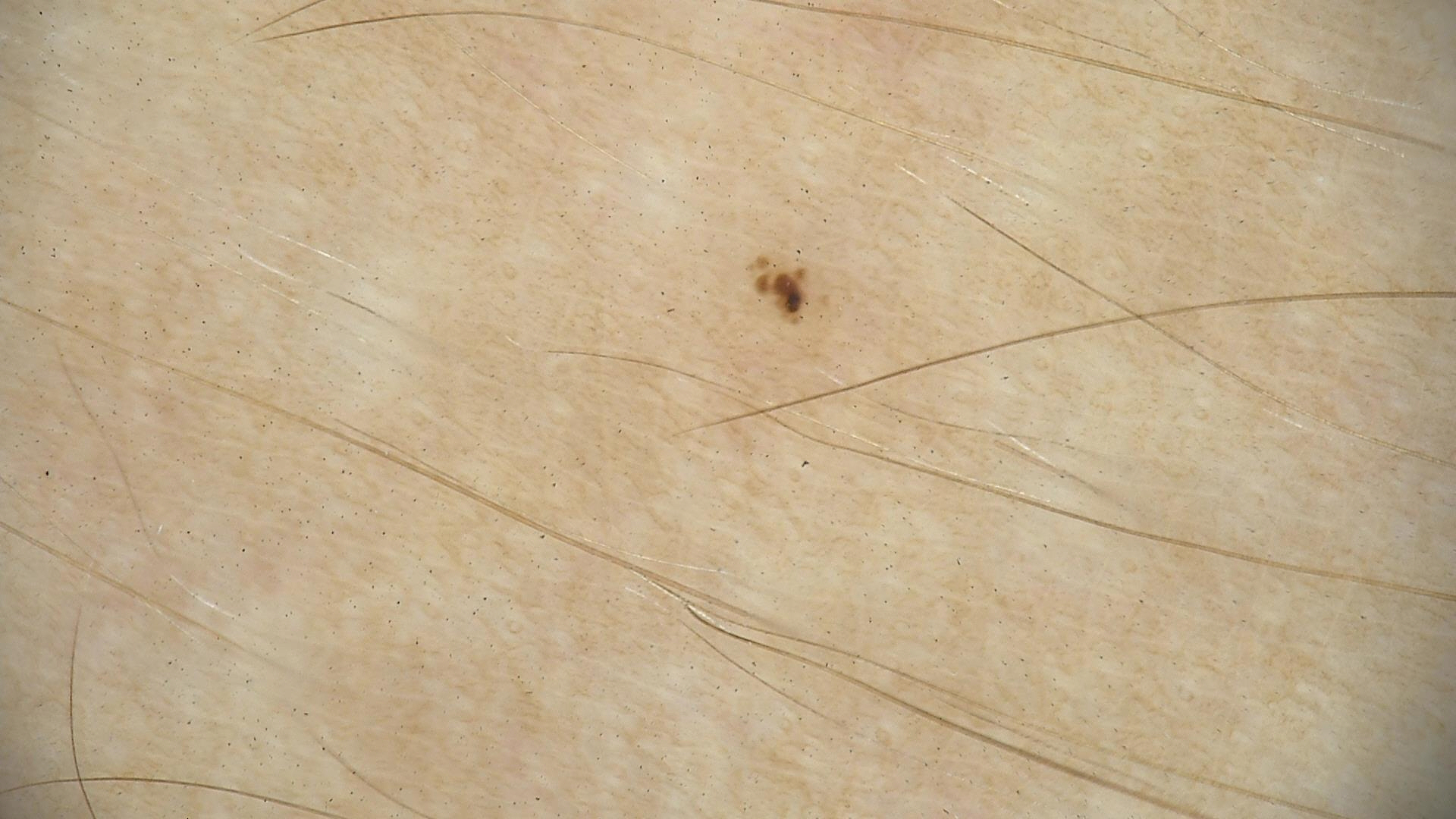The diagnosis was a dysplastic junctional nevus.